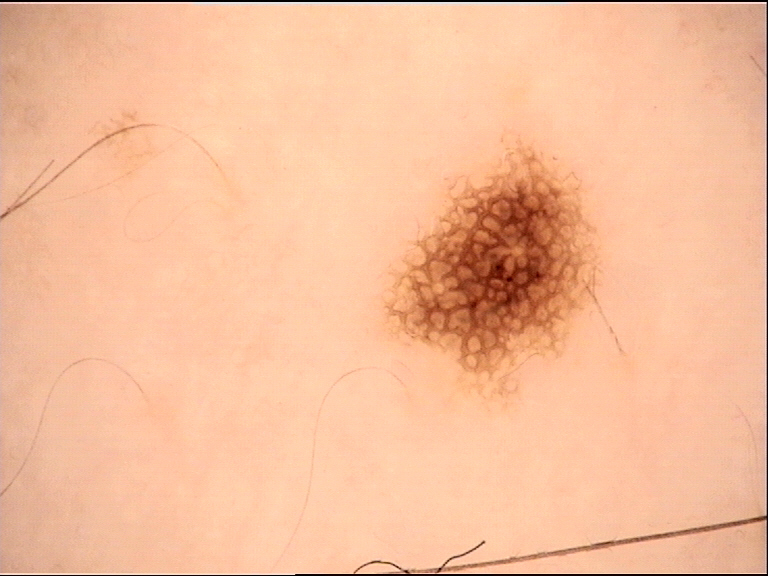image type — dermatoscopy
diagnosis — dysplastic junctional nevus (expert consensus)